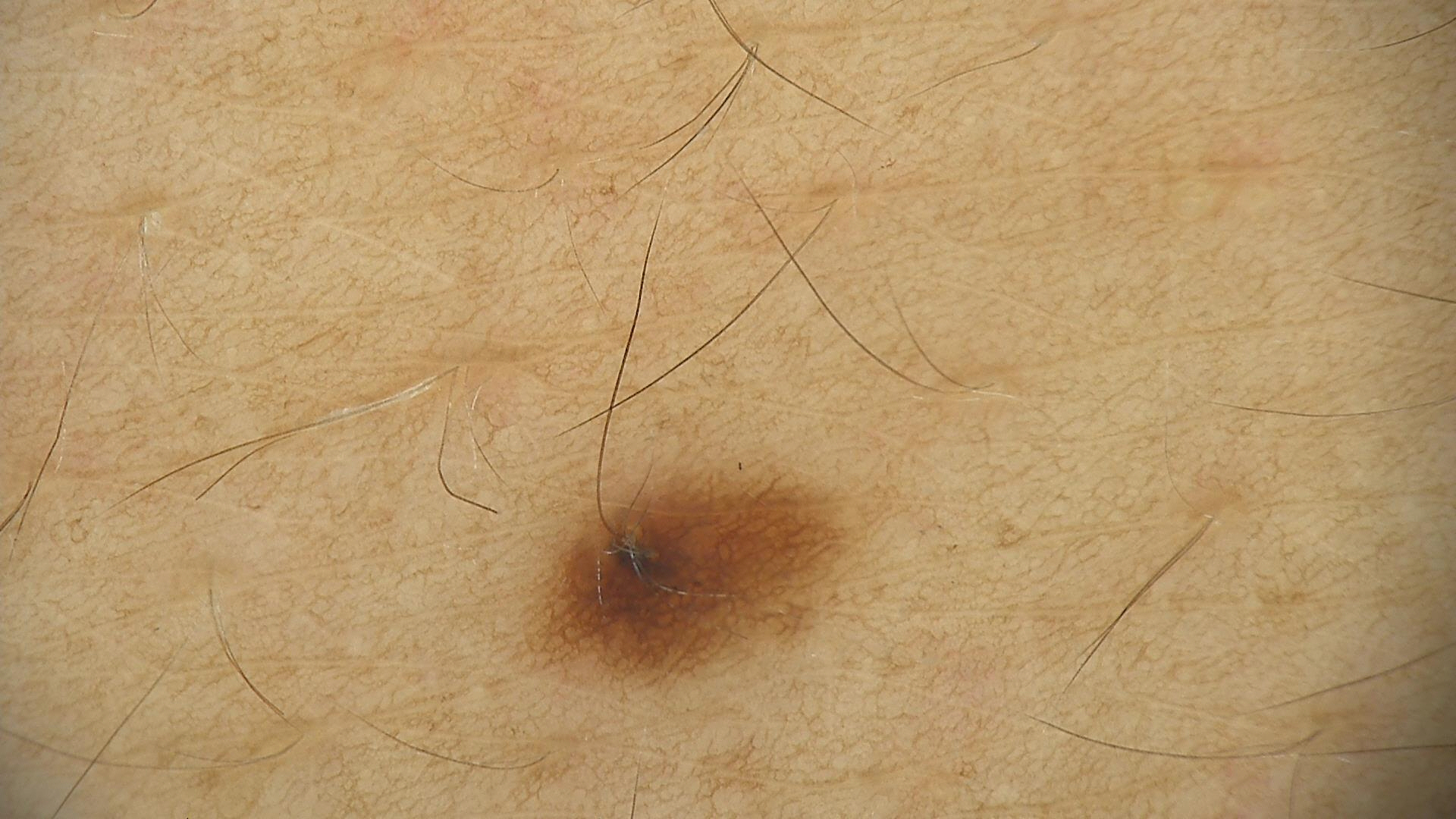Q: What is the diagnosis?
A: dysplastic junctional nevus (expert consensus)